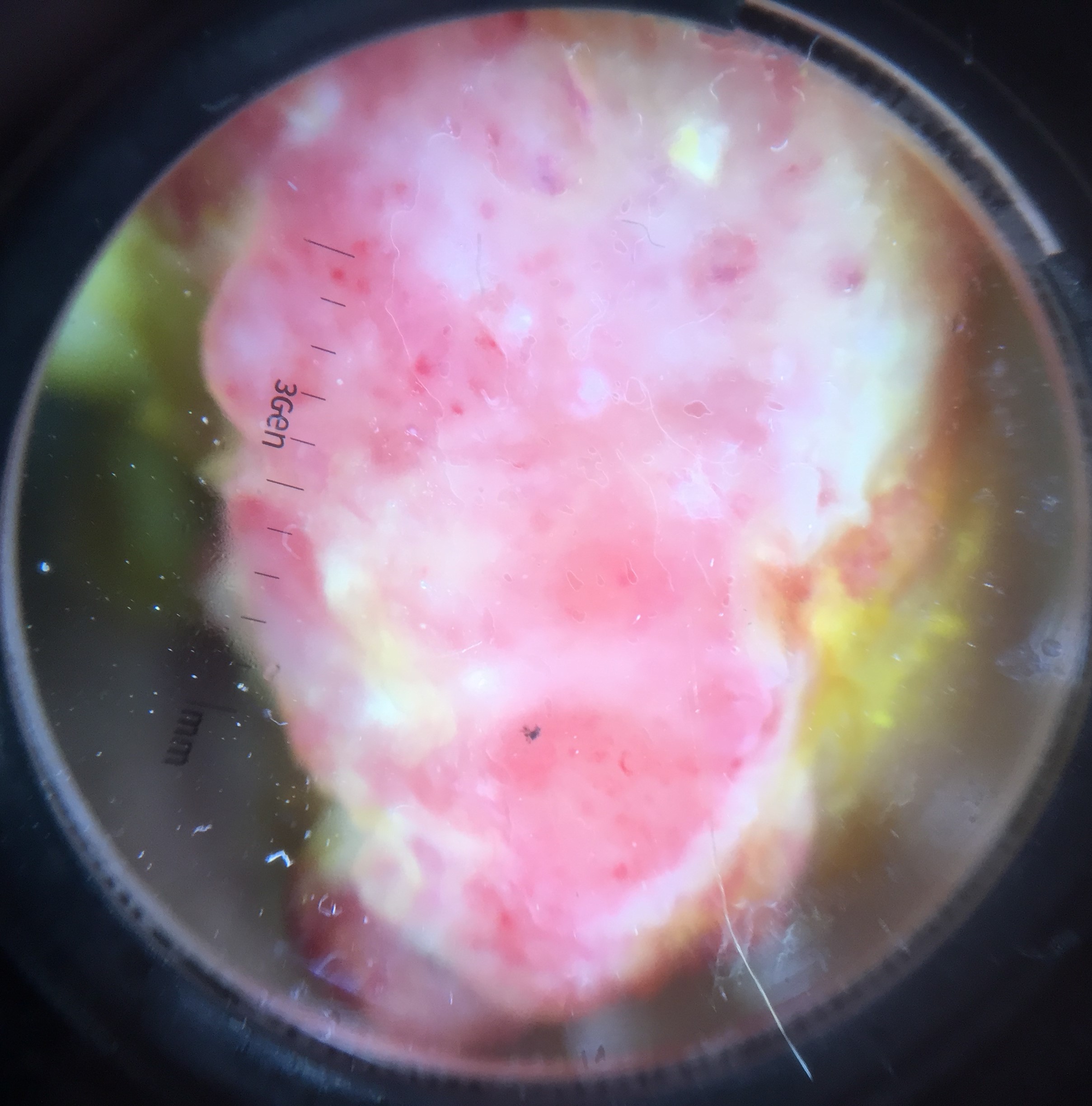Confirmed on histopathology as an acral nodular melanoma.